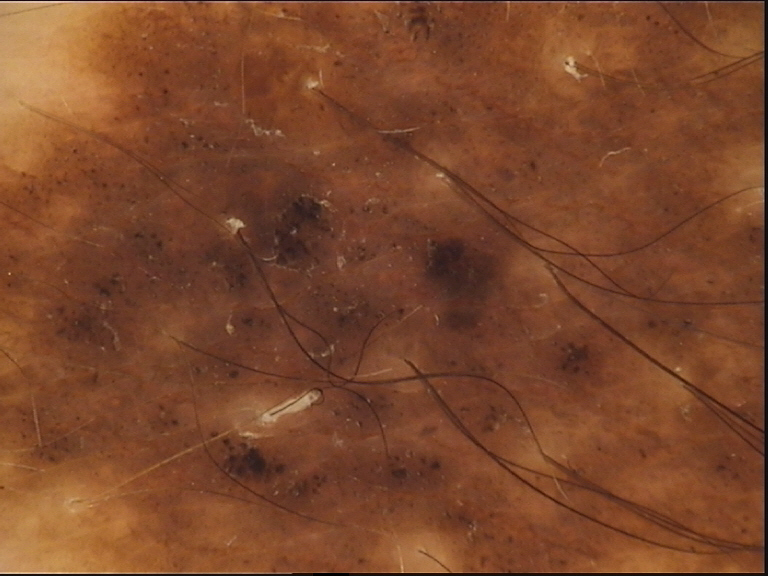Findings:
* image type — dermoscopy
* subtype — banal
* label — congenital compound nevus (expert consensus)